A dermoscopic image of a skin lesion: 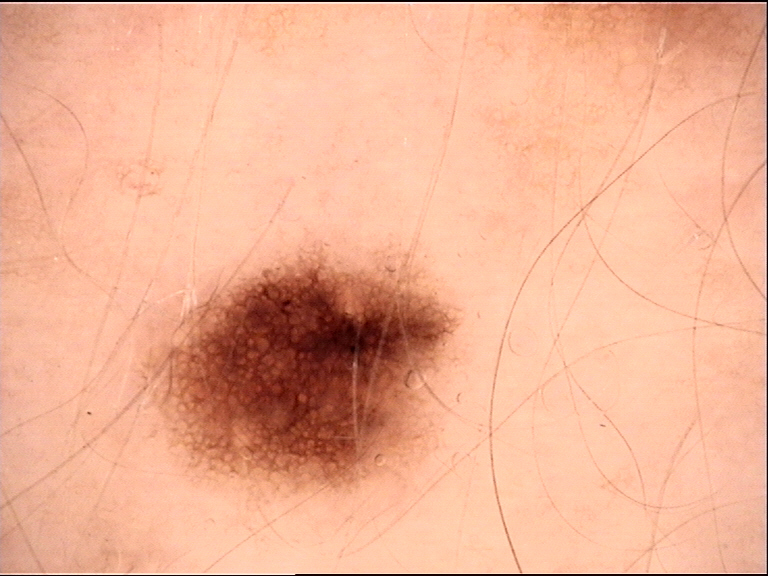* diagnosis: dysplastic junctional nevus (expert consensus)